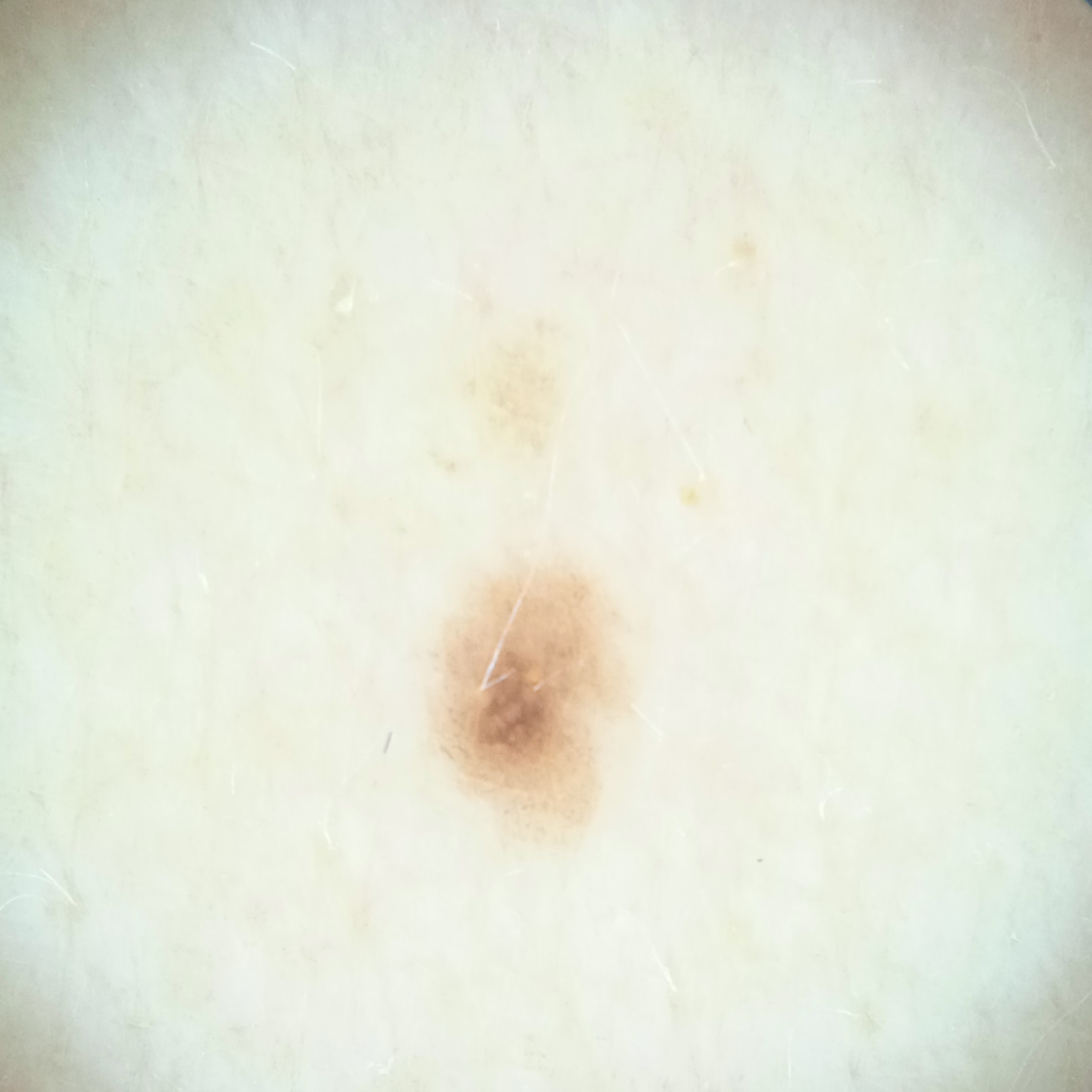Summary:
Acquired for a research image collection, with no referral diagnosis. A female subject 81 years of age. A dermoscopy image of a skin lesion. Located on the back. The lesion measures approximately 2.7 mm.
Assessment:
The diagnostic impression was a melanocytic nevus.